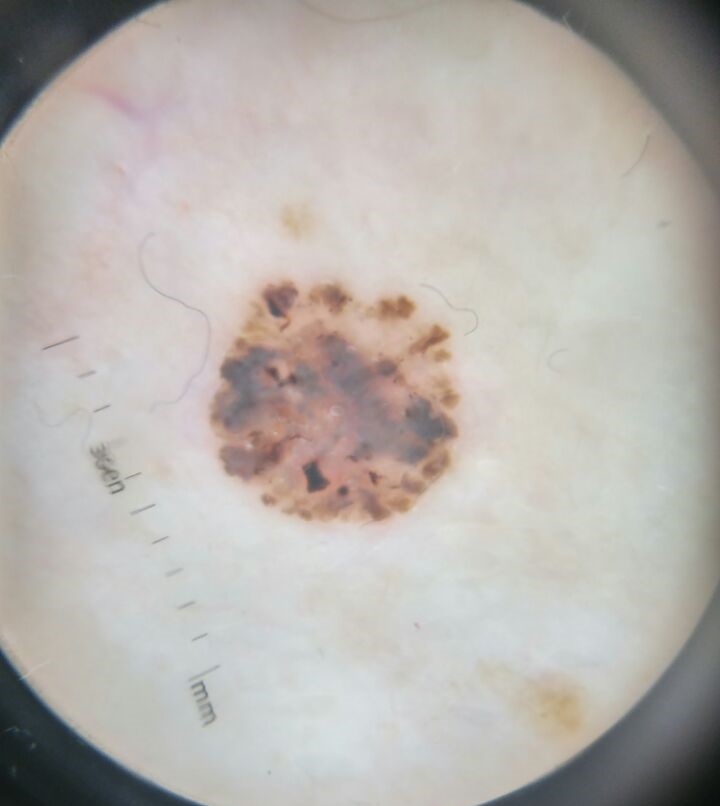– image: dermatoscopy
– label: basal cell carcinoma (biopsy-proven)